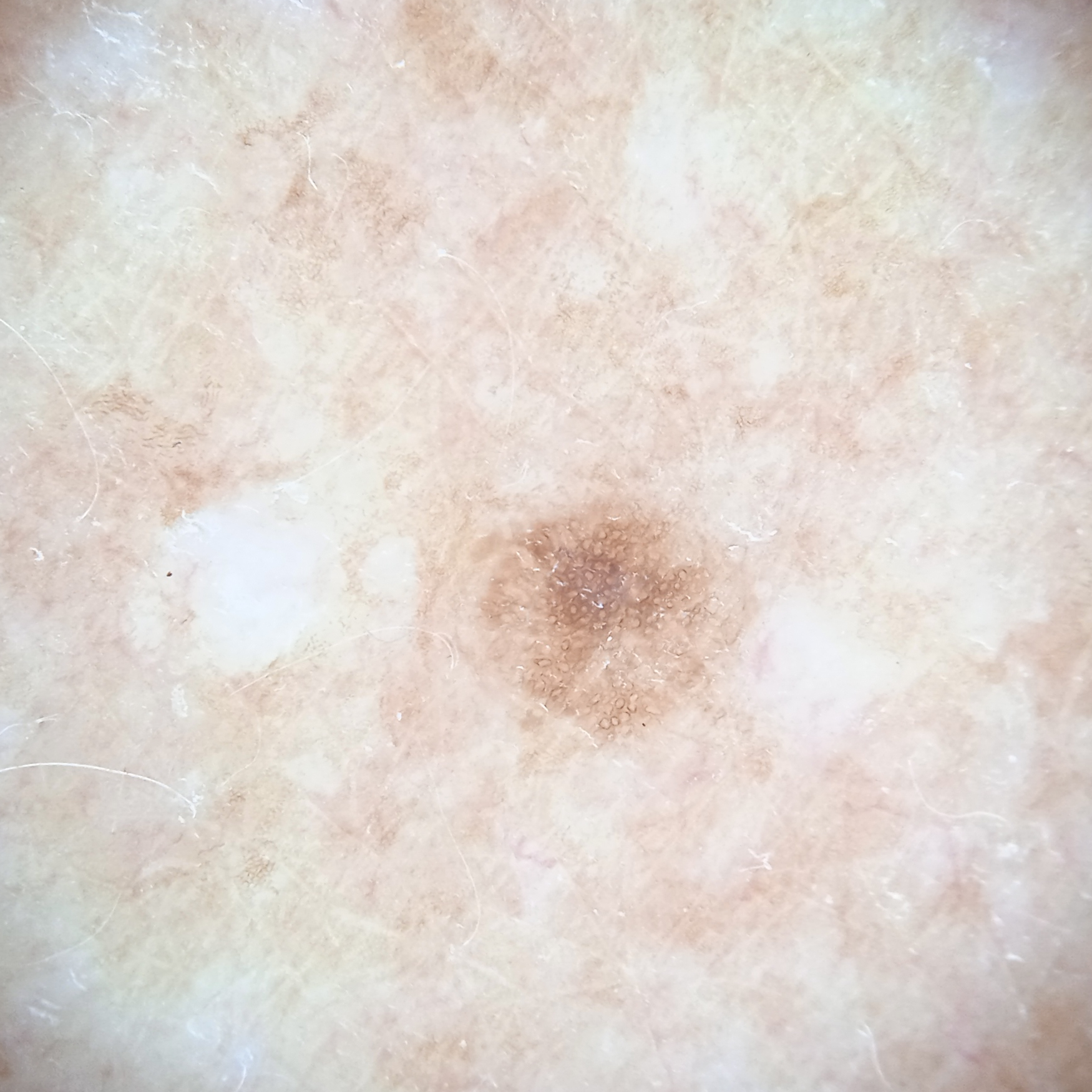- imaging — dermatoscopic image
- patient — female, 75 years of age
- relevant history — a personal history of skin cancer, a personal history of cancer
- referral context — research study (no referral diagnosis)
- sun reaction — skin tans without first burning
- body site — the back
- size — 2.7 mm
- diagnosis — melanocytic nevus (dermatologist consensus)